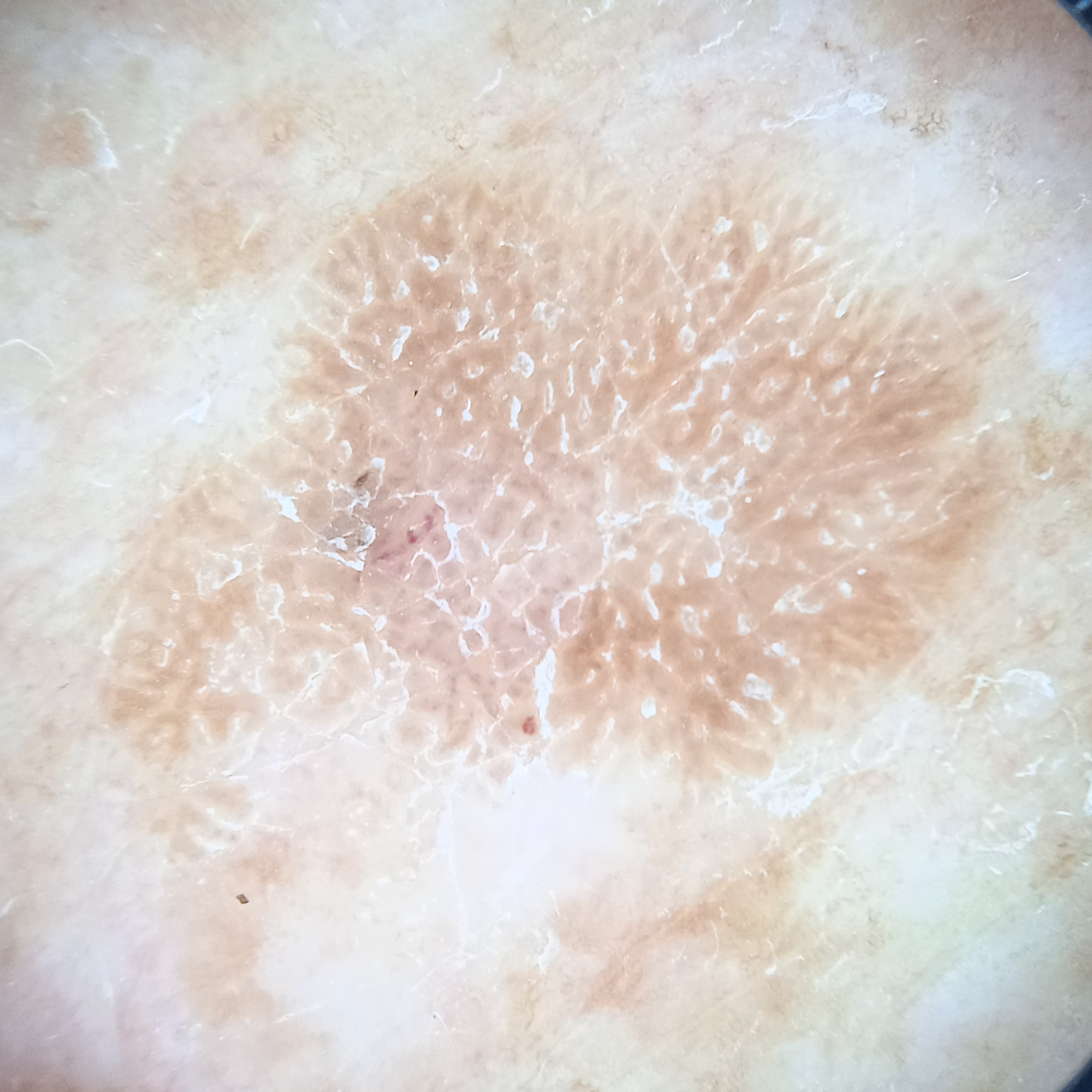{
  "patient": {
    "age": 73,
    "sex": "male"
  },
  "referral": "research study (no referral diagnosis)",
  "image": "dermoscopy",
  "lesion_location": "the back",
  "lesion_size": {
    "diameter_mm": 10.7
  },
  "diagnosis": {
    "name": "seborrheic keratosis",
    "malignancy": "benign"
  }
}